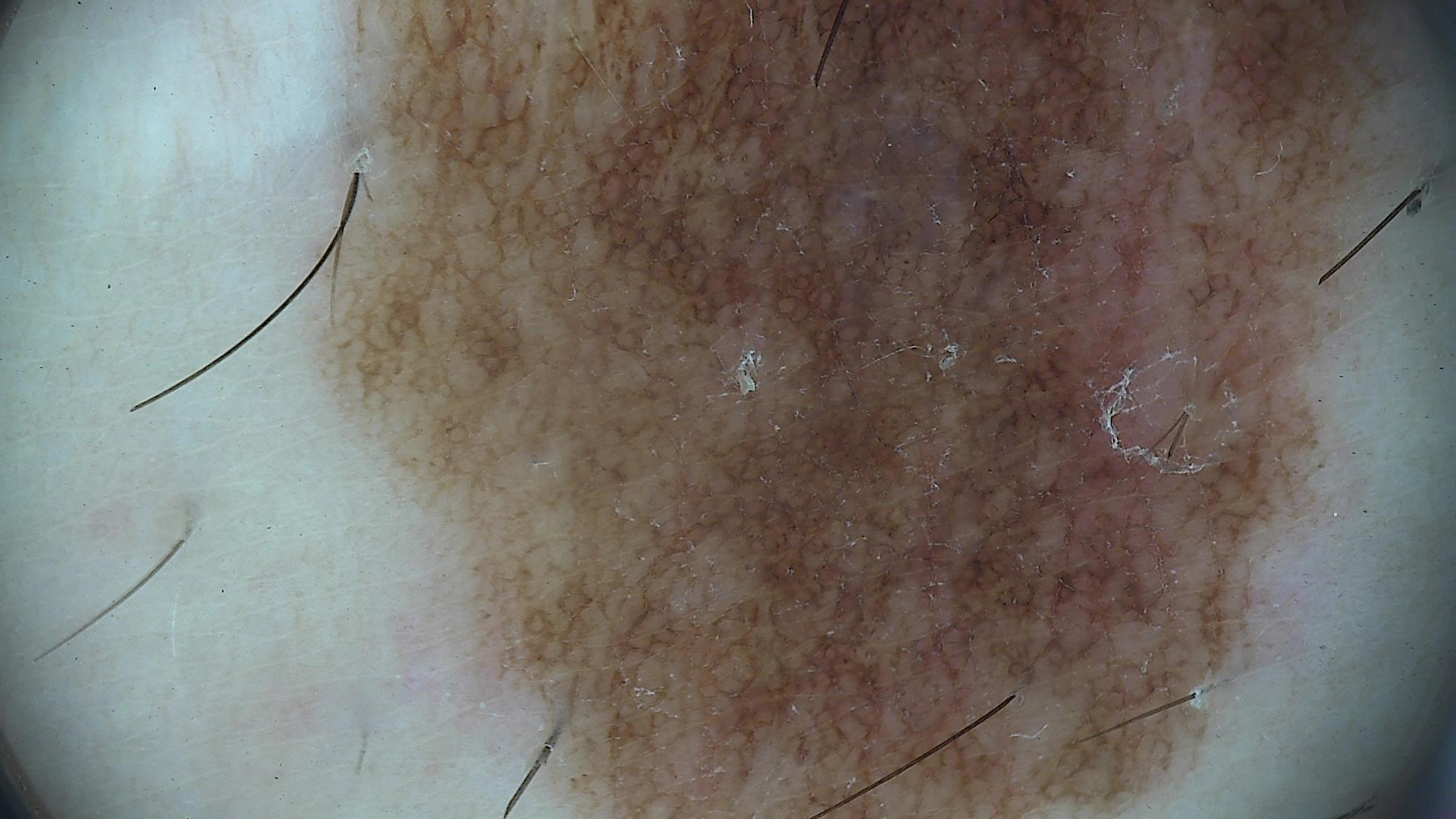image = dermoscopy
class = congenital dysplastic compound nevus (expert consensus)